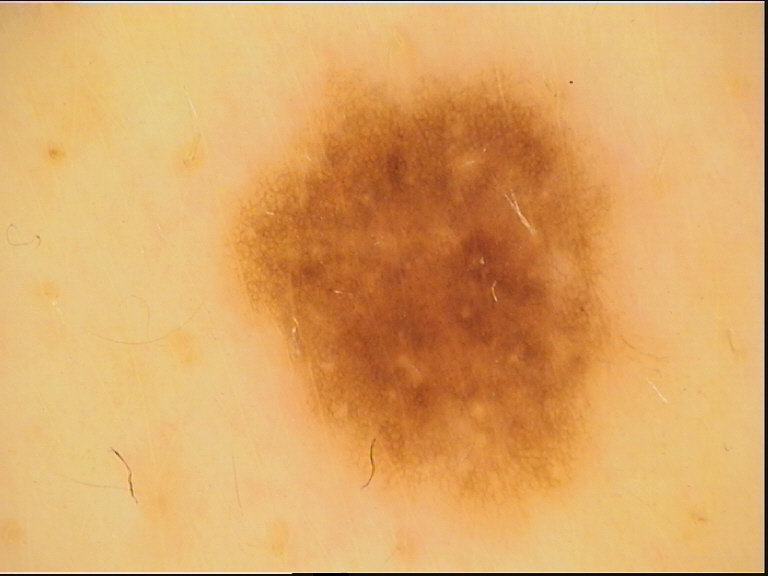The diagnosis was a dysplastic junctional nevus.